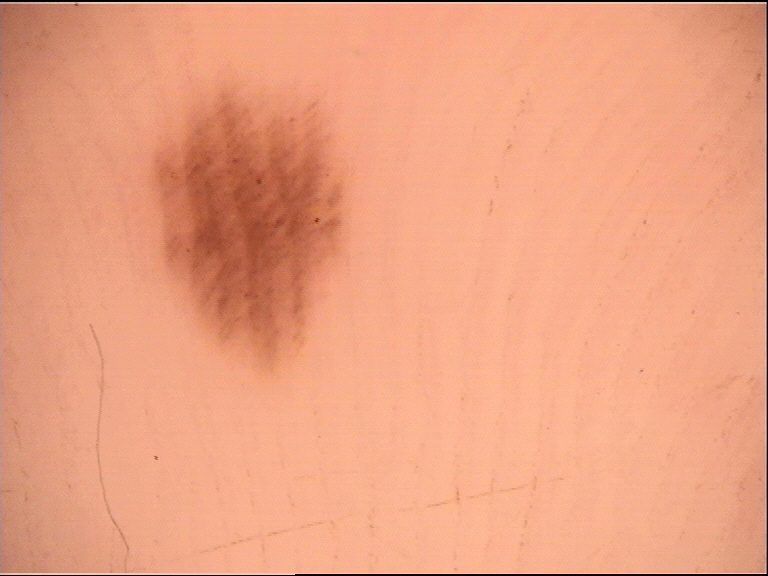Labeled as an acral dysplastic junctional nevus.